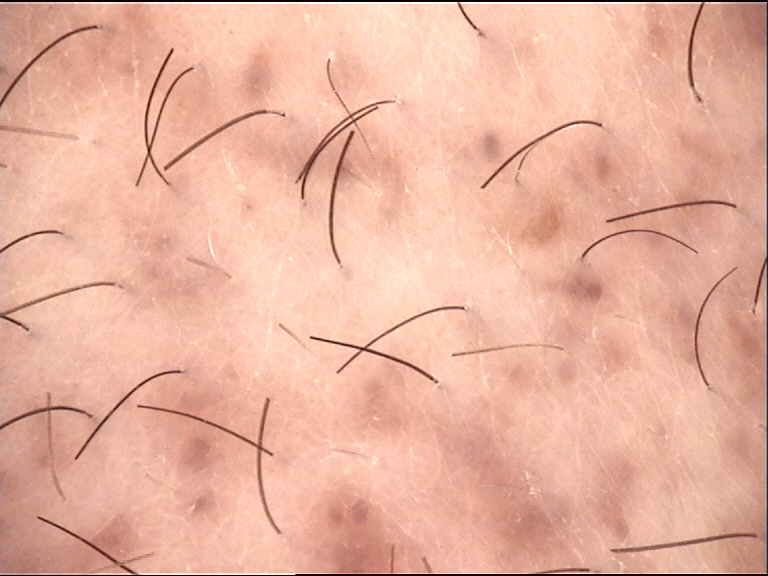modality: dermoscopy, category: banal, diagnostic label: congenital compound nevus (expert consensus).